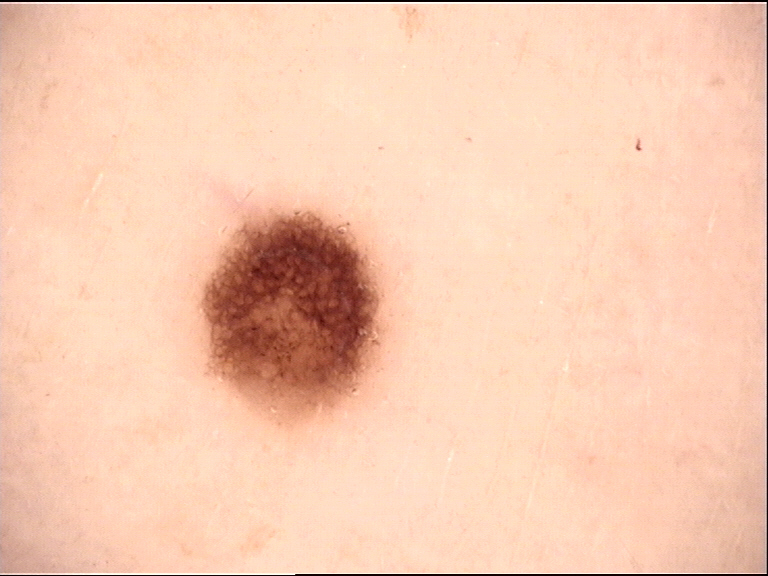modality: dermoscopy, label: dysplastic junctional nevus (expert consensus).